A dermoscopic close-up of a skin lesion:
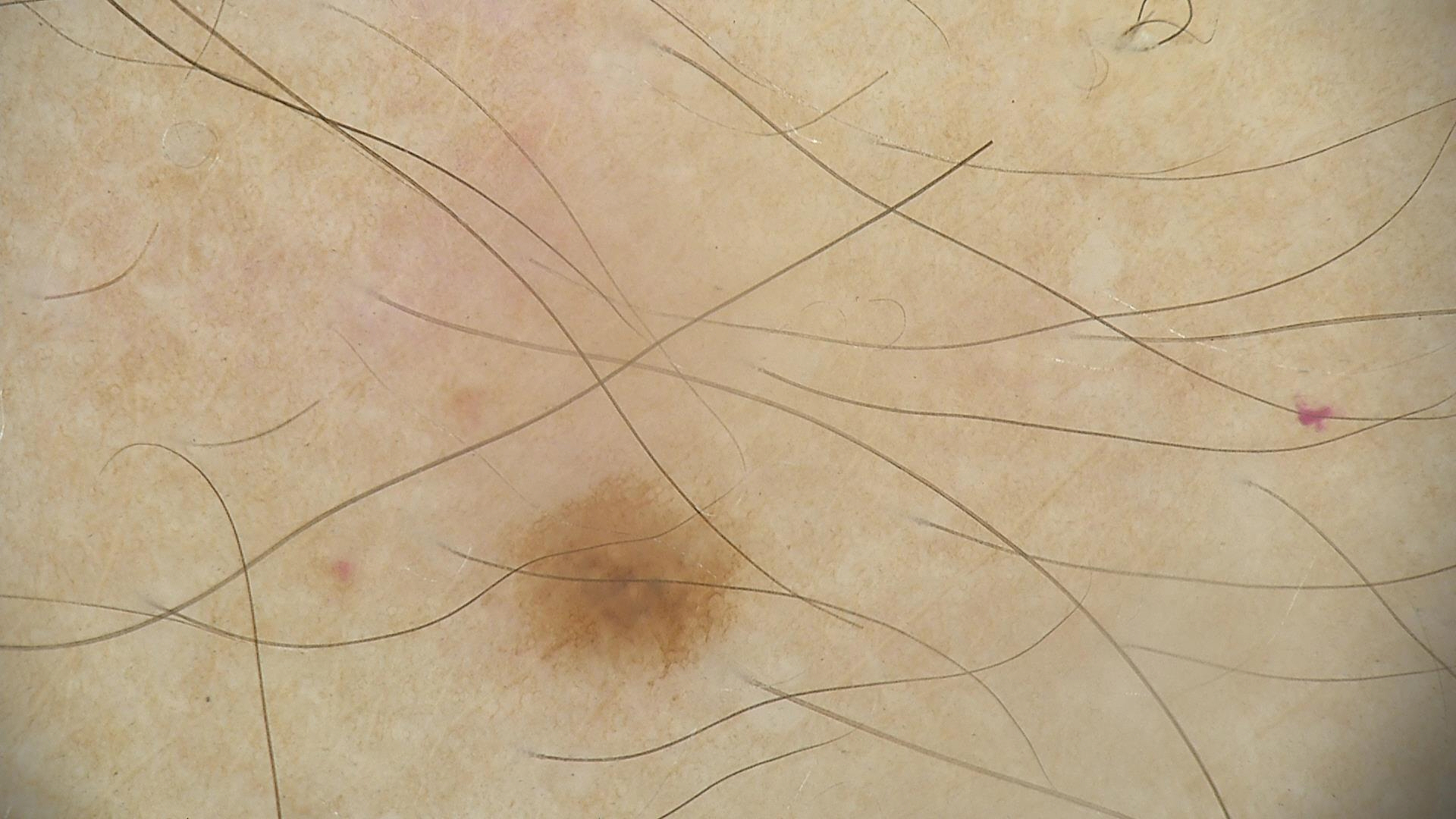{"diagnosis": {"name": "dysplastic junctional nevus", "code": "jd", "malignancy": "benign", "super_class": "melanocytic", "confirmation": "expert consensus"}}